A dermoscopic image of a skin lesion, the subject is a male aged 68-72: 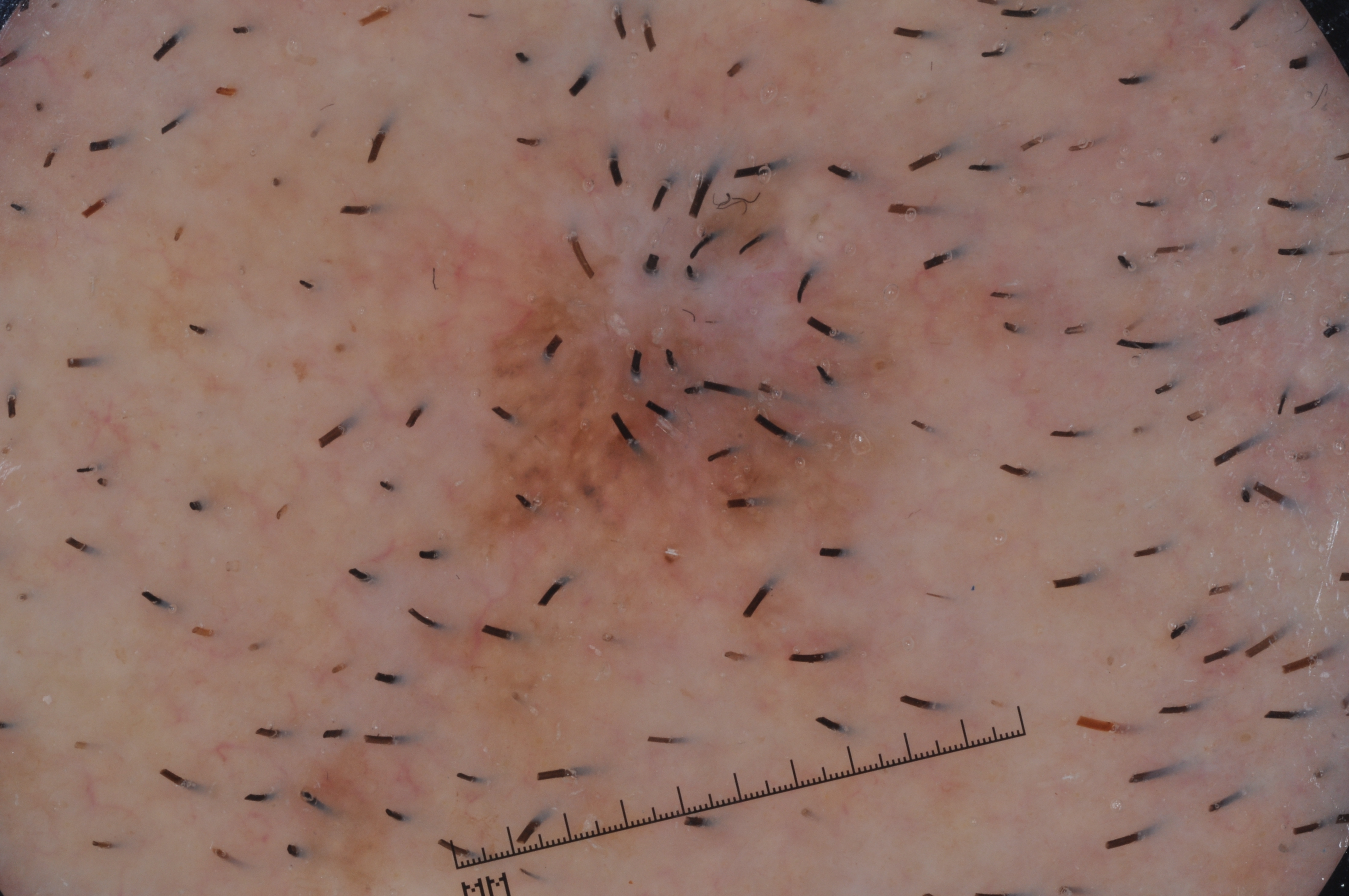{"dermoscopic_features": {"present": [], "absent": ["streaks", "milia-like cysts", "pigment network", "negative network"]}, "lesion_location": {"bbox_xyxy": [400, 120, 1096, 849]}, "diagnosis": {"name": "melanoma", "malignancy": "malignant", "lineage": "melanocytic", "provenance": "histopathology"}}